The contributor notes the condition has been present for more than five years · the patient also reports fatigue and joint pain · reported lesion symptoms include itching, darkening, enlargement, burning, bothersome appearance and bleeding · the contributor is a female aged 60–69 · an image taken at a distance · located on the leg and arm · texture is reported as rough or flaky and raised or bumpy:
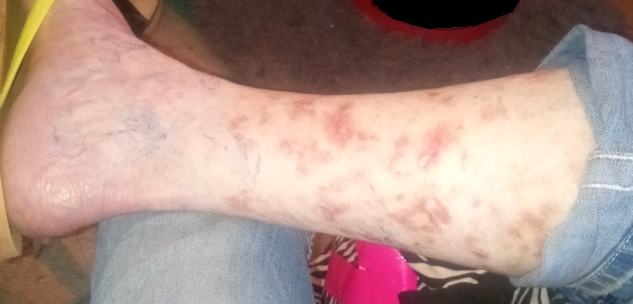Q: What is the dermatologist's impression?
A: Pigmented purpuric eruption (weight 0.50); Stasis Dermatitis (weight 0.50)